A clinical close-up photograph of a skin lesion; a subject in their mid-40s: 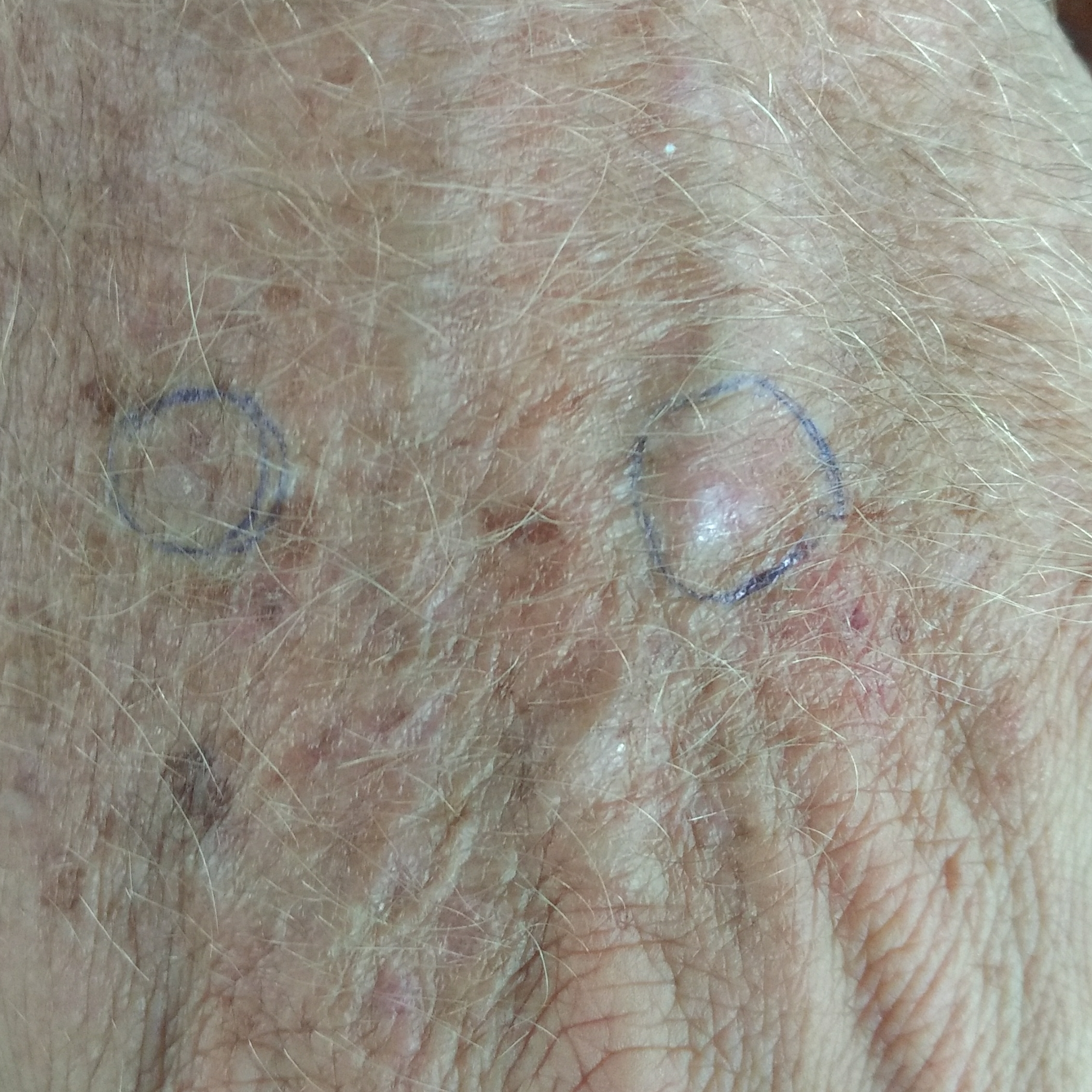anatomic site = a hand
patient-reported symptoms = elevation, itching / no growth
impression = actinic keratosis (clinical consensus)